A dermatoscopic image of a skin lesion:
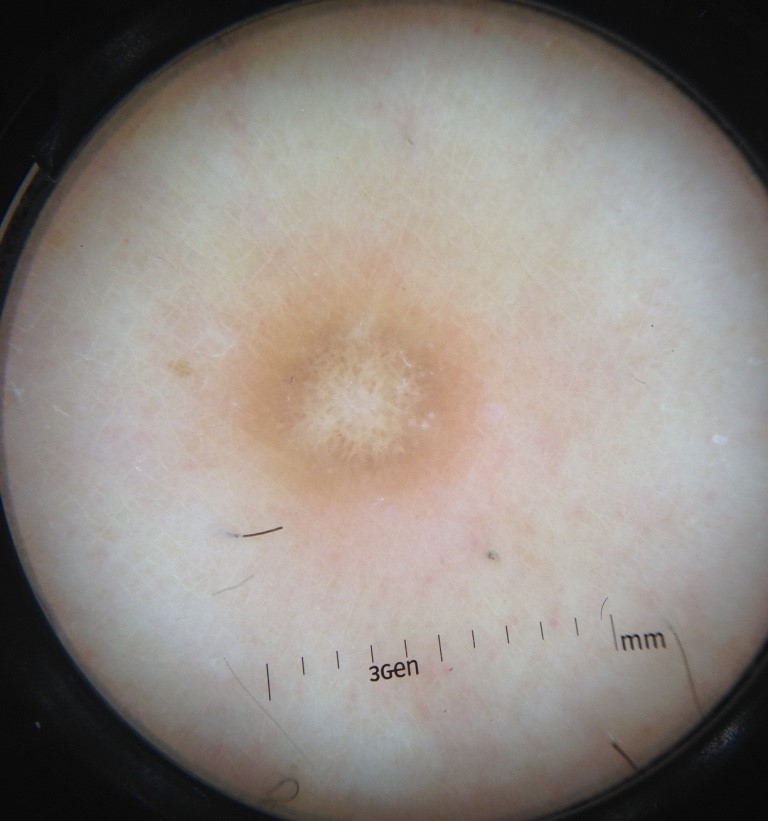class: dermatofibroma (expert consensus).